A dermoscopic photograph of a skin lesion: 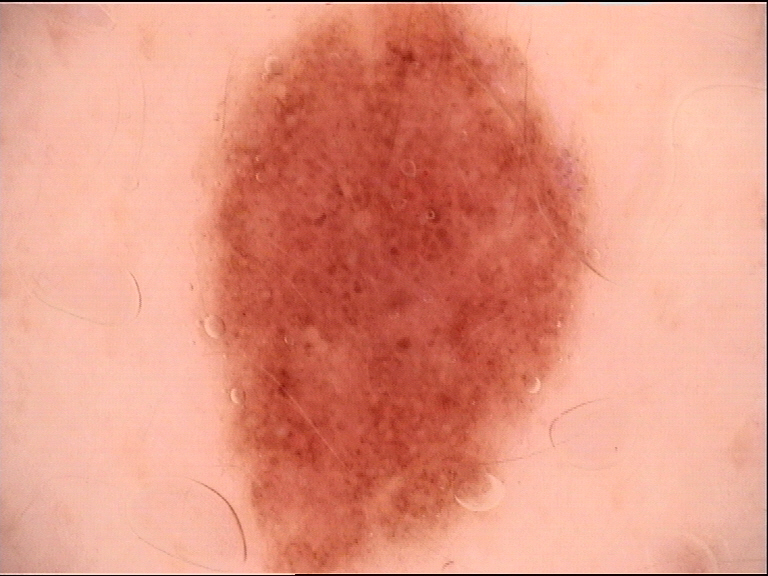| feature | finding |
|---|---|
| diagnosis | dysplastic compound nevus (expert consensus) |